A patient 56 years of age · a clinical photograph showing a skin lesion — 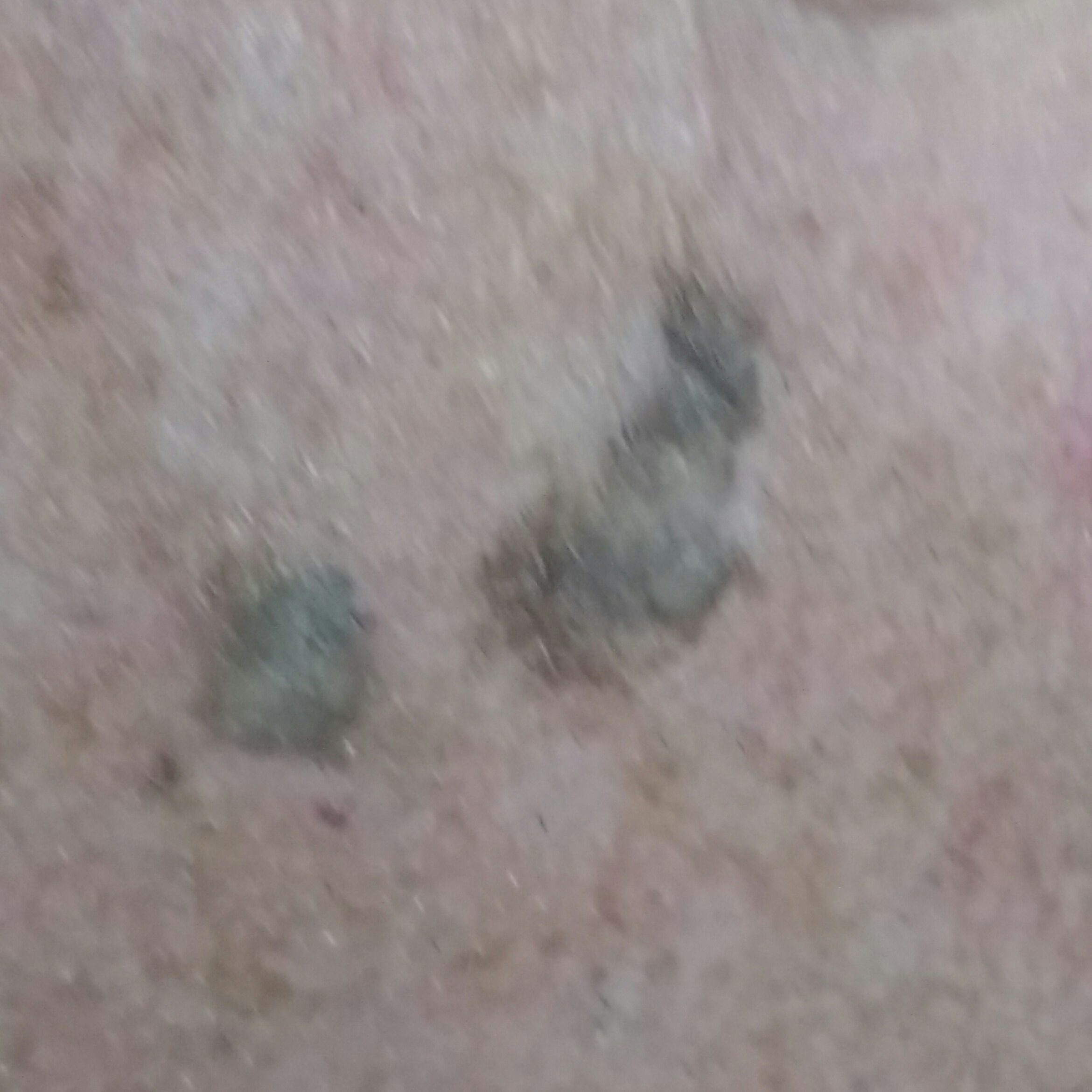site: the face; patient-reported symptoms: growth / no itching; diagnostic label: seborrheic keratosis (clinical consensus).